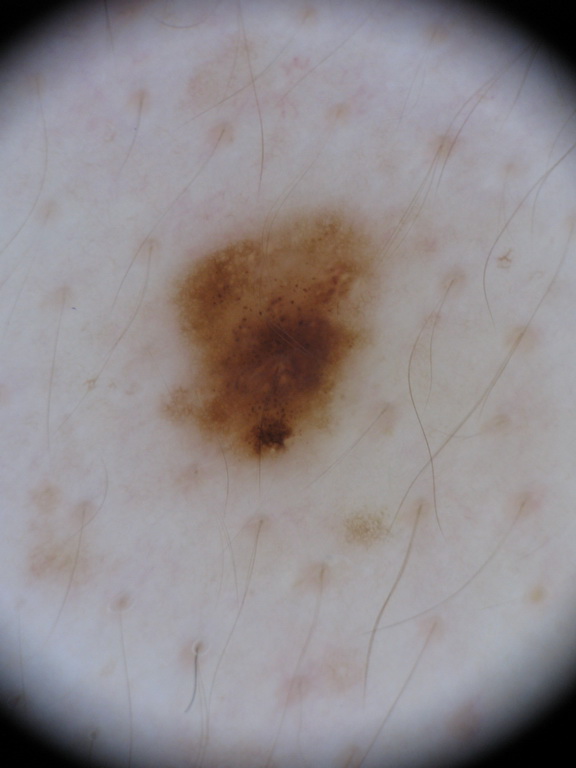{
  "image": {
    "modality": "dermoscopy"
  },
  "lesion_extent": {
    "approx_field_fraction_pct": 10
  },
  "lesion_location": {
    "bbox_xyxy": [
      162,
      207,
      380,
      467
    ]
  },
  "dermoscopic_features": {
    "present": [
      "pigment network",
      "globules"
    ],
    "absent": [
      "negative network",
      "milia-like cysts",
      "streaks"
    ]
  },
  "diagnosis": {
    "name": "melanocytic nevus",
    "malignancy": "benign",
    "lineage": "melanocytic",
    "provenance": "clinical"
  }
}